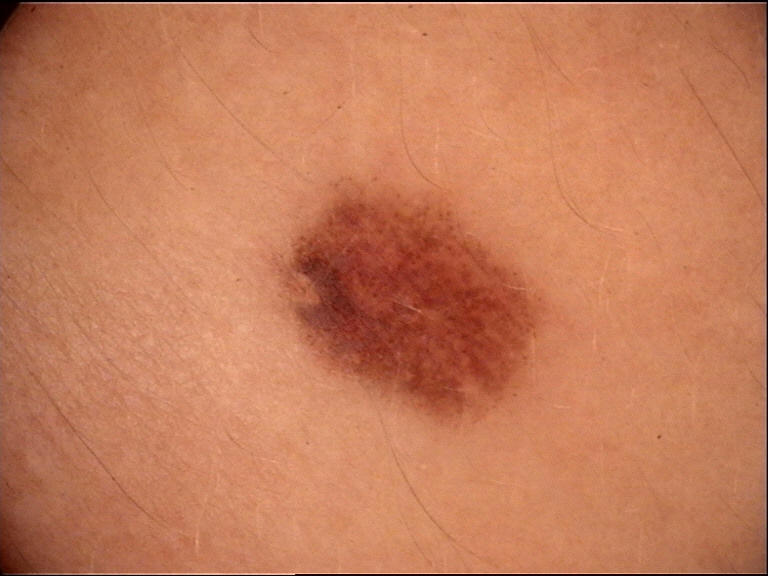A skin lesion imaged with a dermatoscope. Consistent with a dysplastic compound nevus.